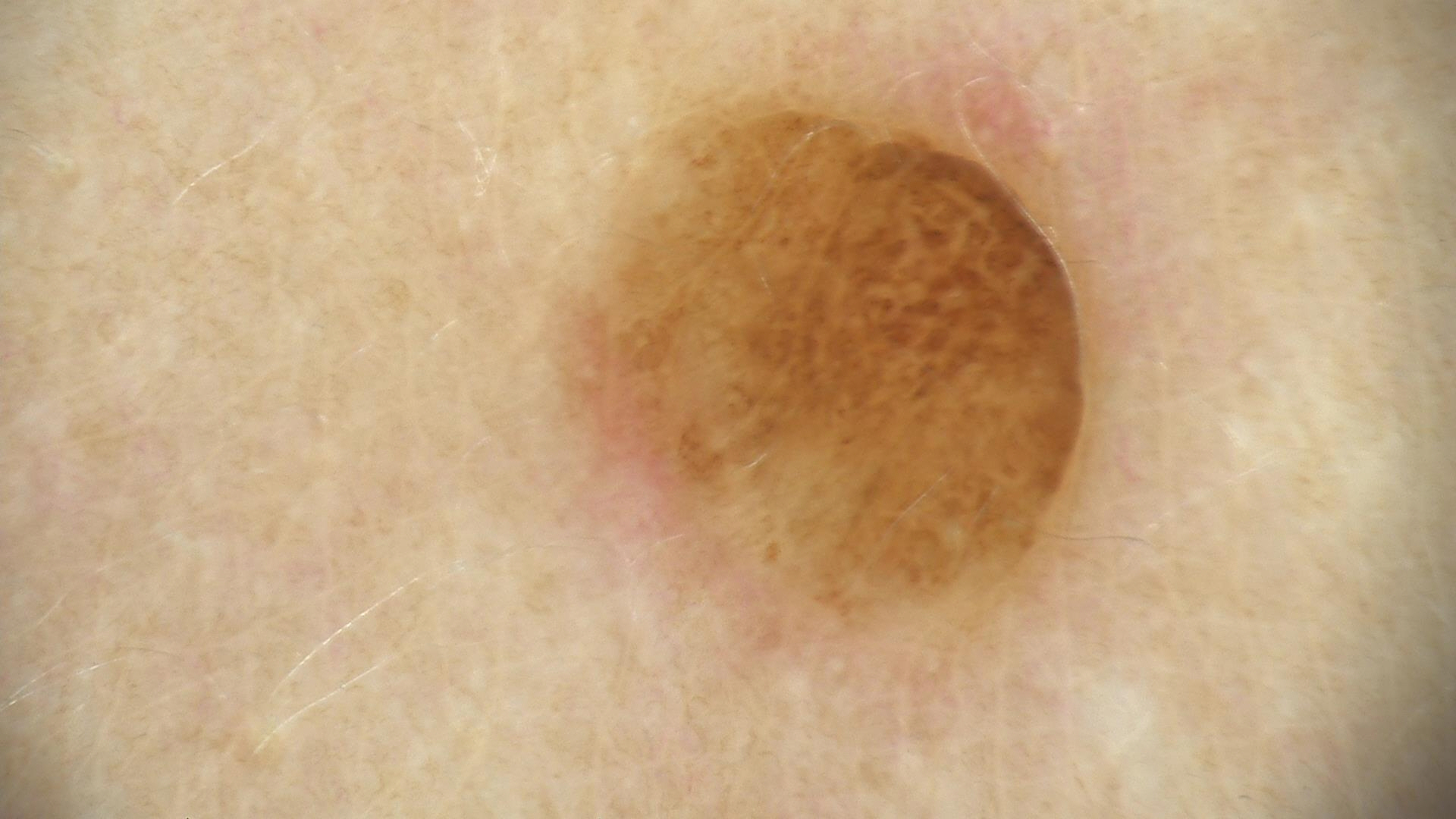The morphology is that of a banal lesion.
The diagnosis was a dermal nevus.